A dermatoscopic image of a skin lesion: 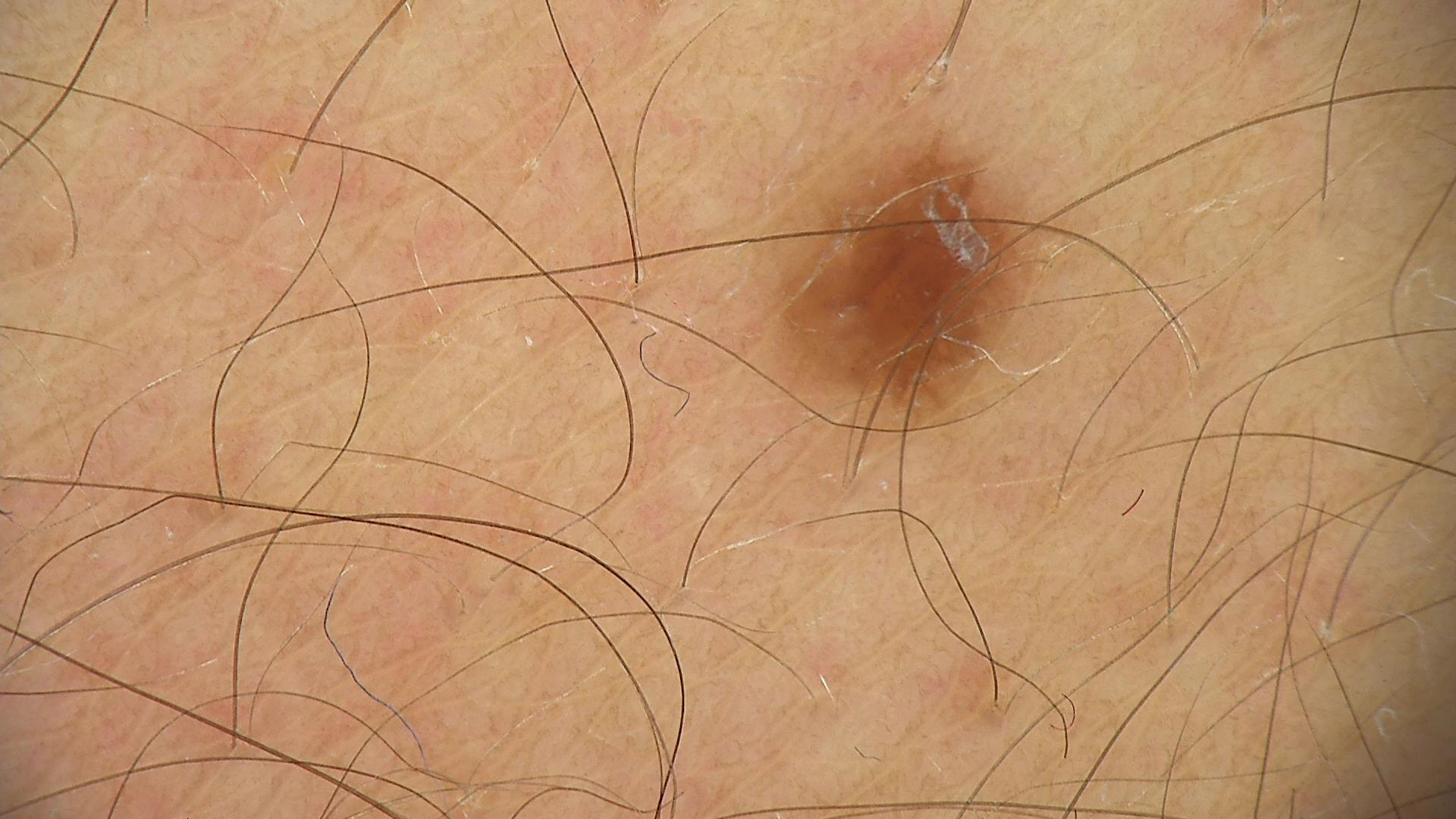• diagnostic label · junctional nevus (expert consensus)